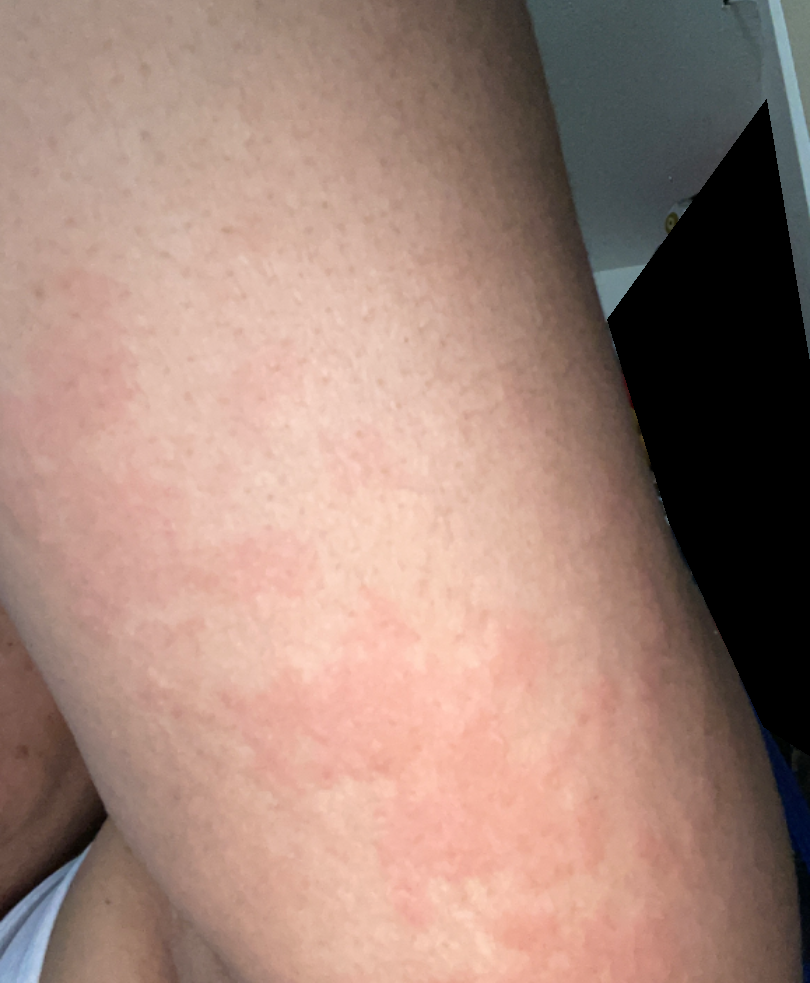The contributor reports the condition has been present for less than one week. The affected area is the arm and leg. No associated systemic symptoms reported. Symptoms reported: enlargement and itching. Fitzpatrick II; lay graders estimated 2 on the Monk skin tone scale. The contributor reports the lesion is raised or bumpy. A close-up photograph. The patient described the issue as a rash. Urticaria (0.78); Eczema (0.11); Allergic Contact Dermatitis (0.11).